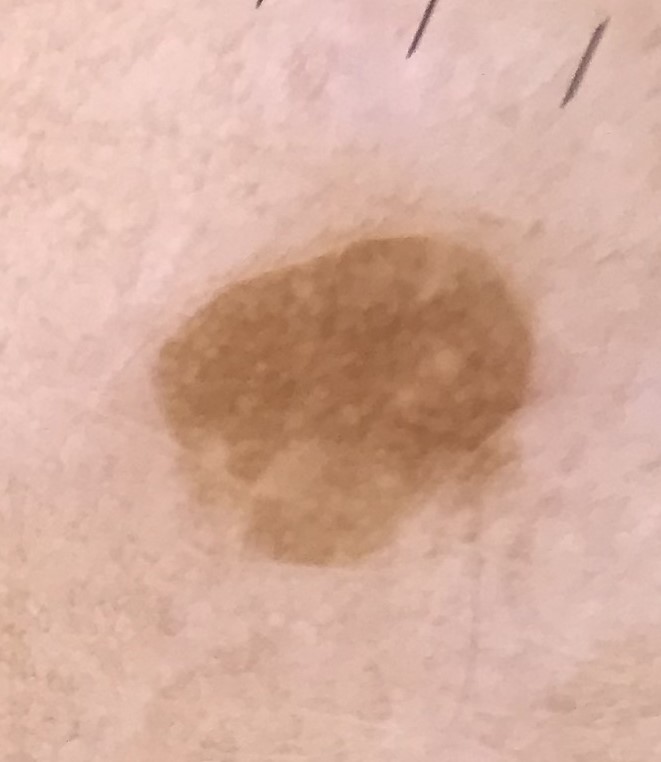Q: What kind of image is this?
A: dermoscopy
Q: What is the diagnosis?
A: seborrheic keratosis (expert consensus)